The patient is a female aged 60–69; this is a close-up image; the affected area is the back of the hand, arm and leg: 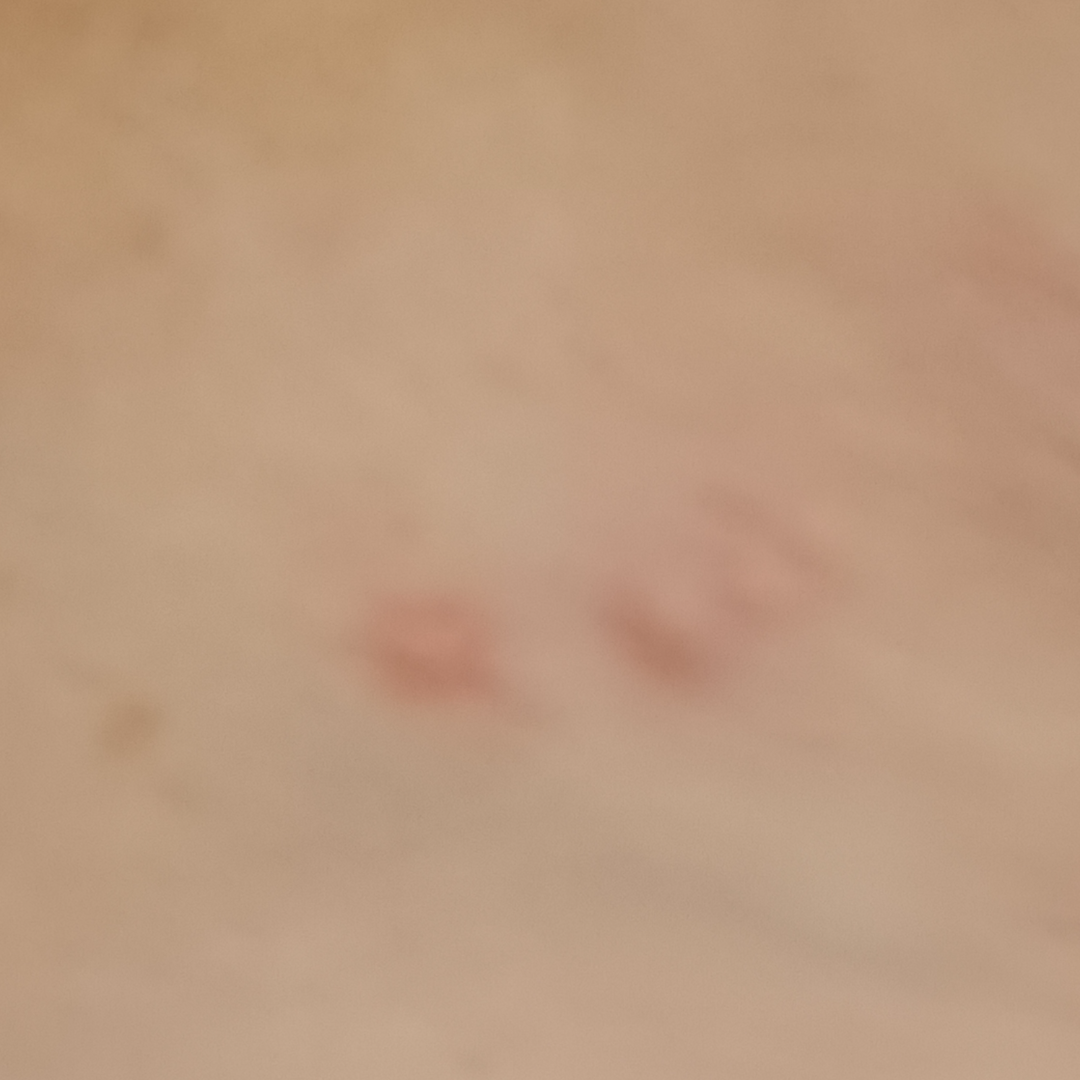Case summary:
• assessment — ungradable on photographic review
• patient-reported symptoms — itching
• skin tone — Fitzpatrick skin type II
• symptom duration — about one day